A smartphone photograph of a skin lesion · the patient was assessed as FST II · a female patient age 46.
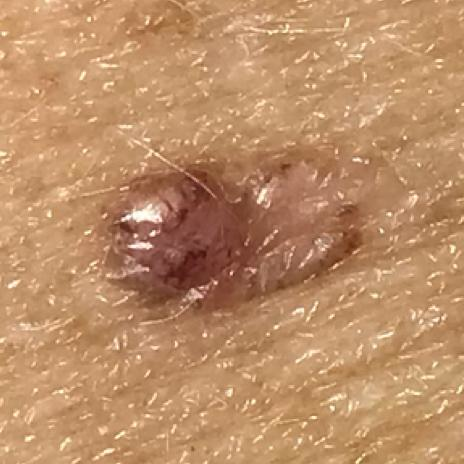Case:
- body site · the back
- lesion size · approx. 10 × 5 mm
- patient-reported symptoms · growth, elevation, itching / no change in appearance, no pain
- pathology · basal cell carcinoma (biopsy-proven)